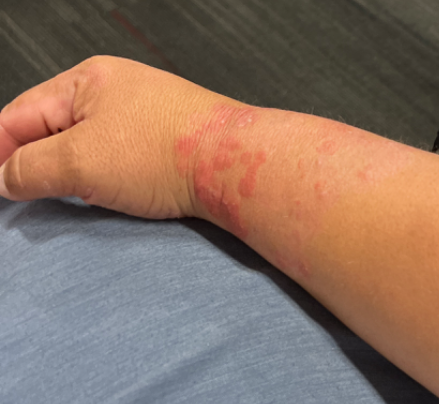Q: How was the photo taken?
A: at a distance
Q: What is the dermatologist's impression?
A: consistent with Acute dermatitis, NOS